The patient was assessed as Fitzpatrick II; a clinical photograph showing a skin lesion in context; a female patient aged 33-37.
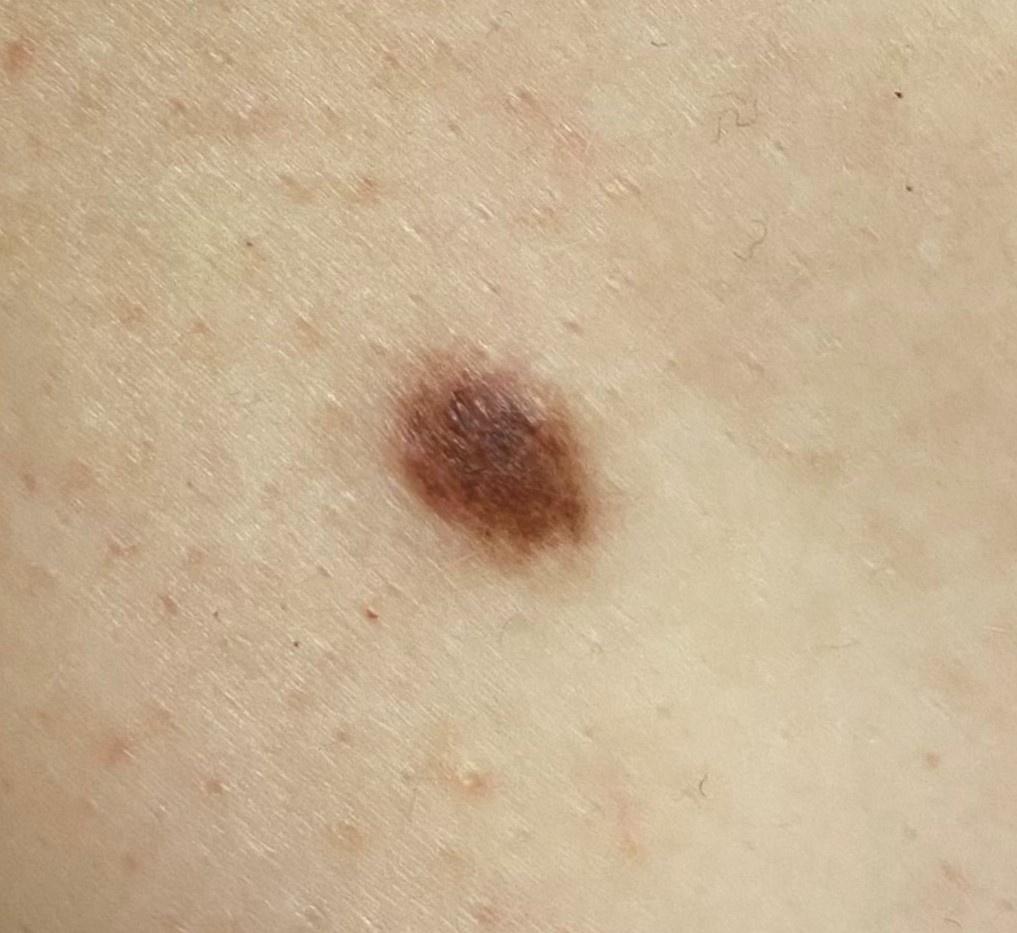The lesion involves the trunk.
Expert review favored a benign, melanocytic lesion — a nevus.